Dermoscopy of a skin lesion:
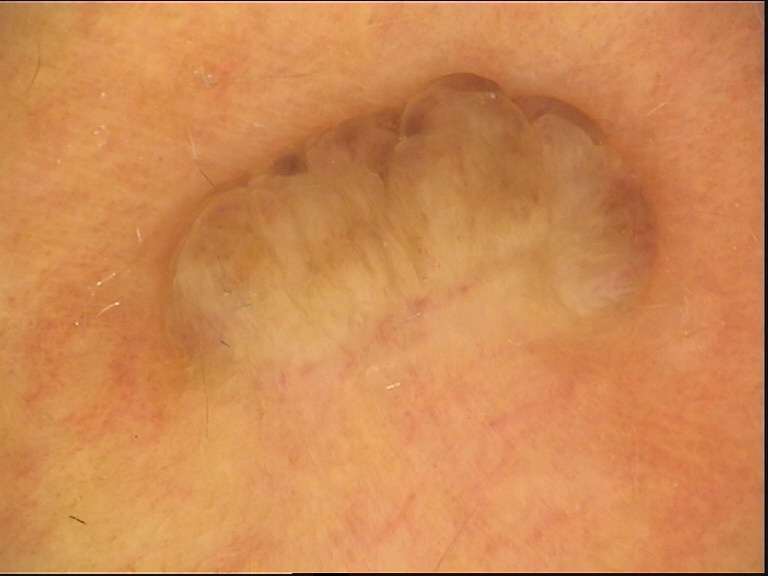Case:
The morphology is that of a banal lesion.
Conclusion:
The diagnostic label was a dermal nevus.